Dermoscopy of a skin lesion; a female patient, aged around 60 — 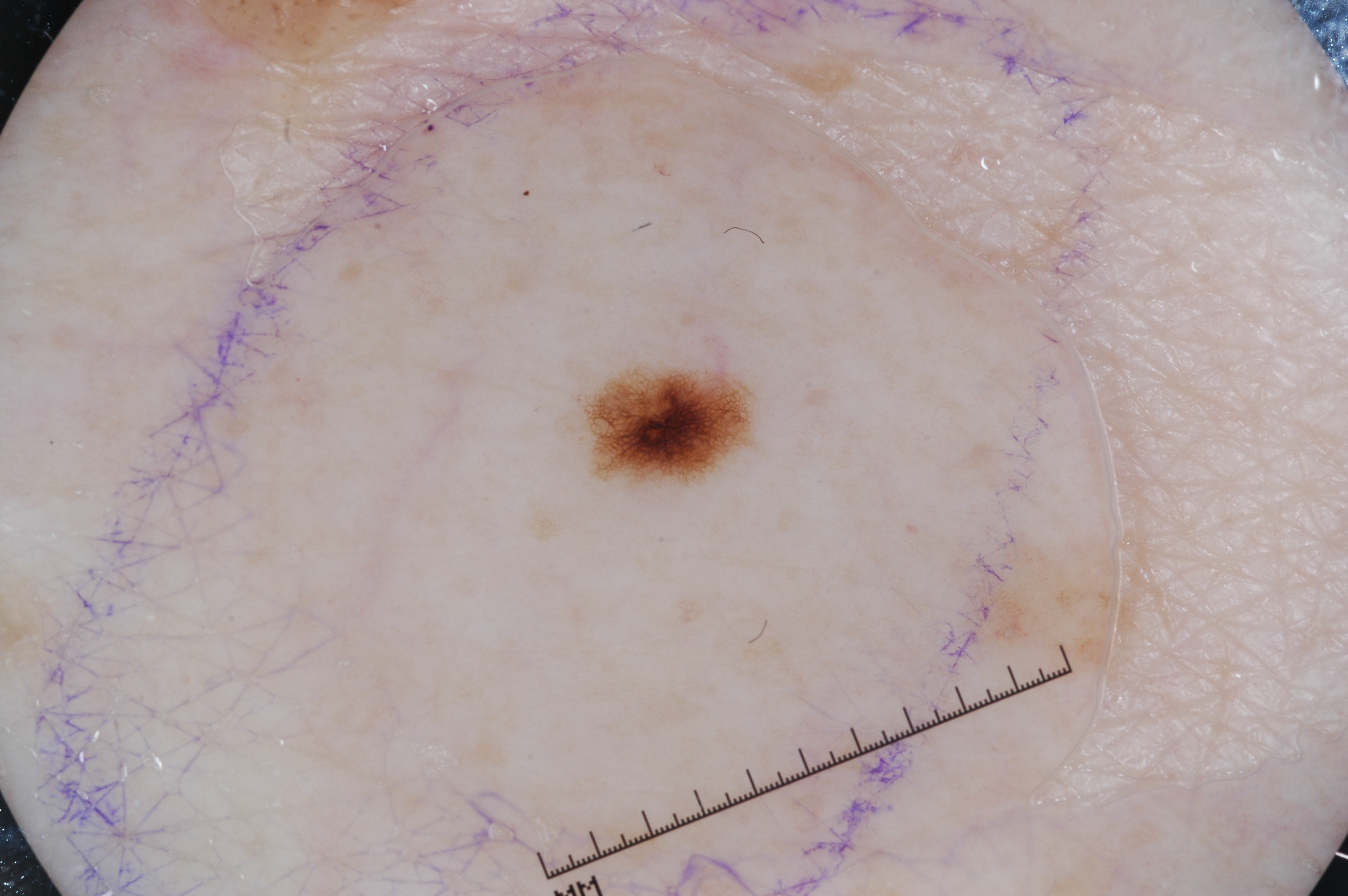features = pigment network; absent: negative network, streaks, and milia-like cysts | bounding box = [590,371,747,483] | lesion extent = ~1% of the field | diagnosis = a melanocytic nevus, a benign skin lesion.